The photo was captured at a distance; the subject is a female aged 50–59; the affected area is the arm, leg and back of the torso: 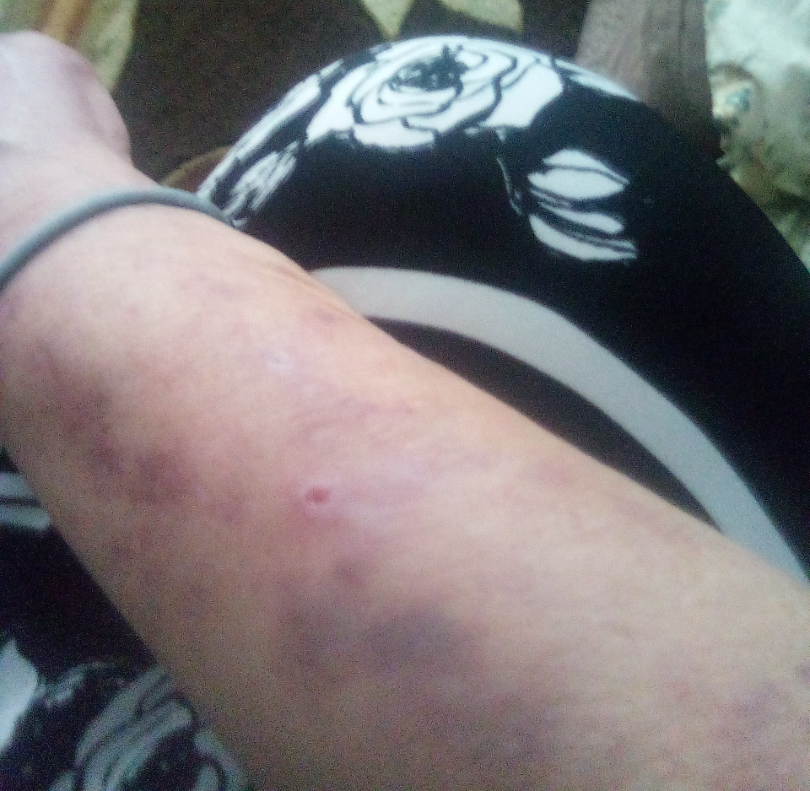assessment: ungradable on photographic review
present for: three to twelve months
lesion texture: raised or bumpy
patient's own categorization: acne
lesion symptoms: itching, bothersome appearance, pain and bleeding